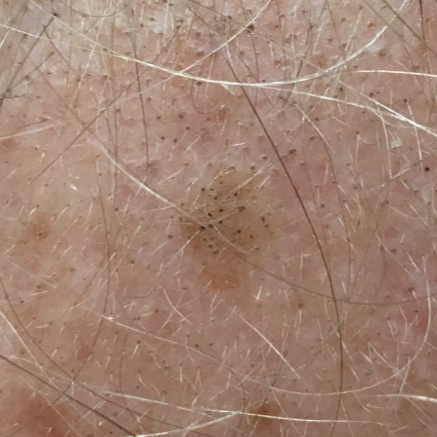Case summary:
A smartphone photograph of a skin lesion. The lesion is located on the scalp.
Impression:
Diagnosed by dermatologist consensus as a benign skin lesion — a seborrheic keratosis.